A skin lesion imaged with a dermatoscope.
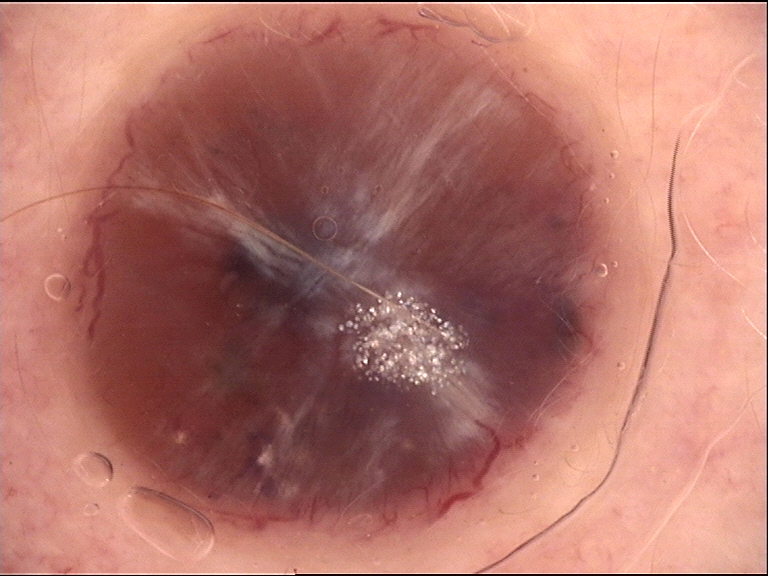Case:
The architecture is that of a keratinocytic lesion.
Conclusion:
Histopathology confirmed a skin cancer — a basal cell carcinoma.